The photo was captured at an angle — 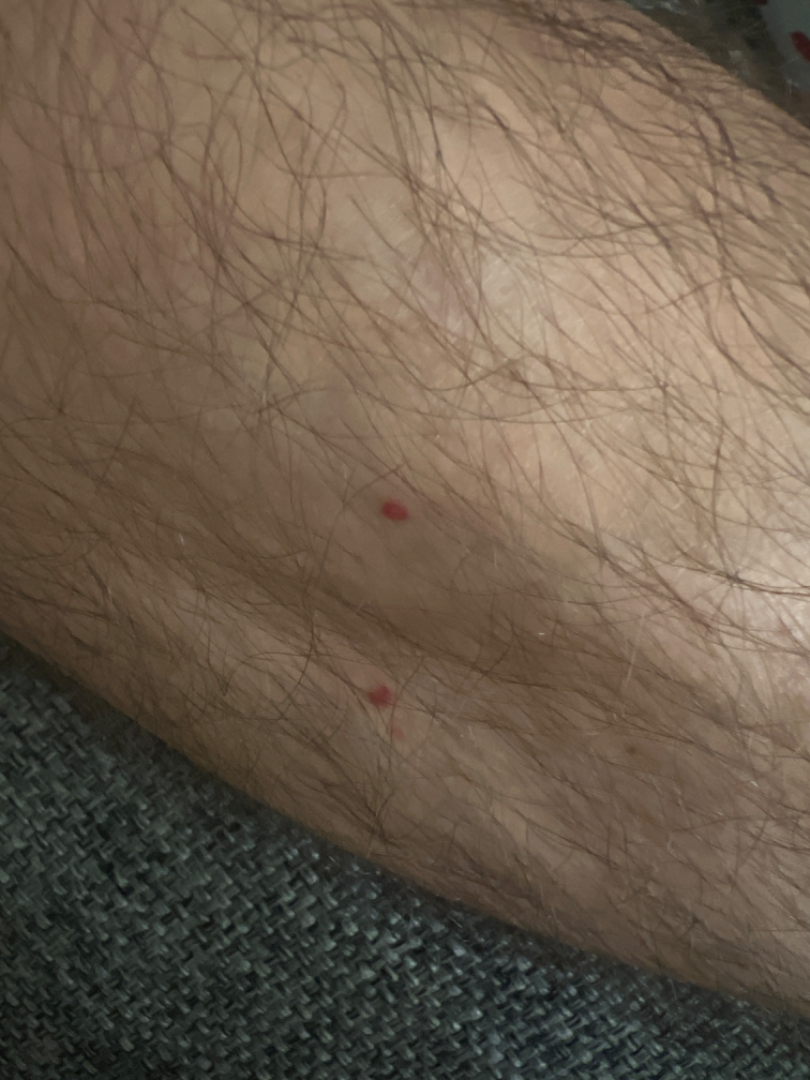The reviewing dermatologist was unable to assign a differential diagnosis from the image.